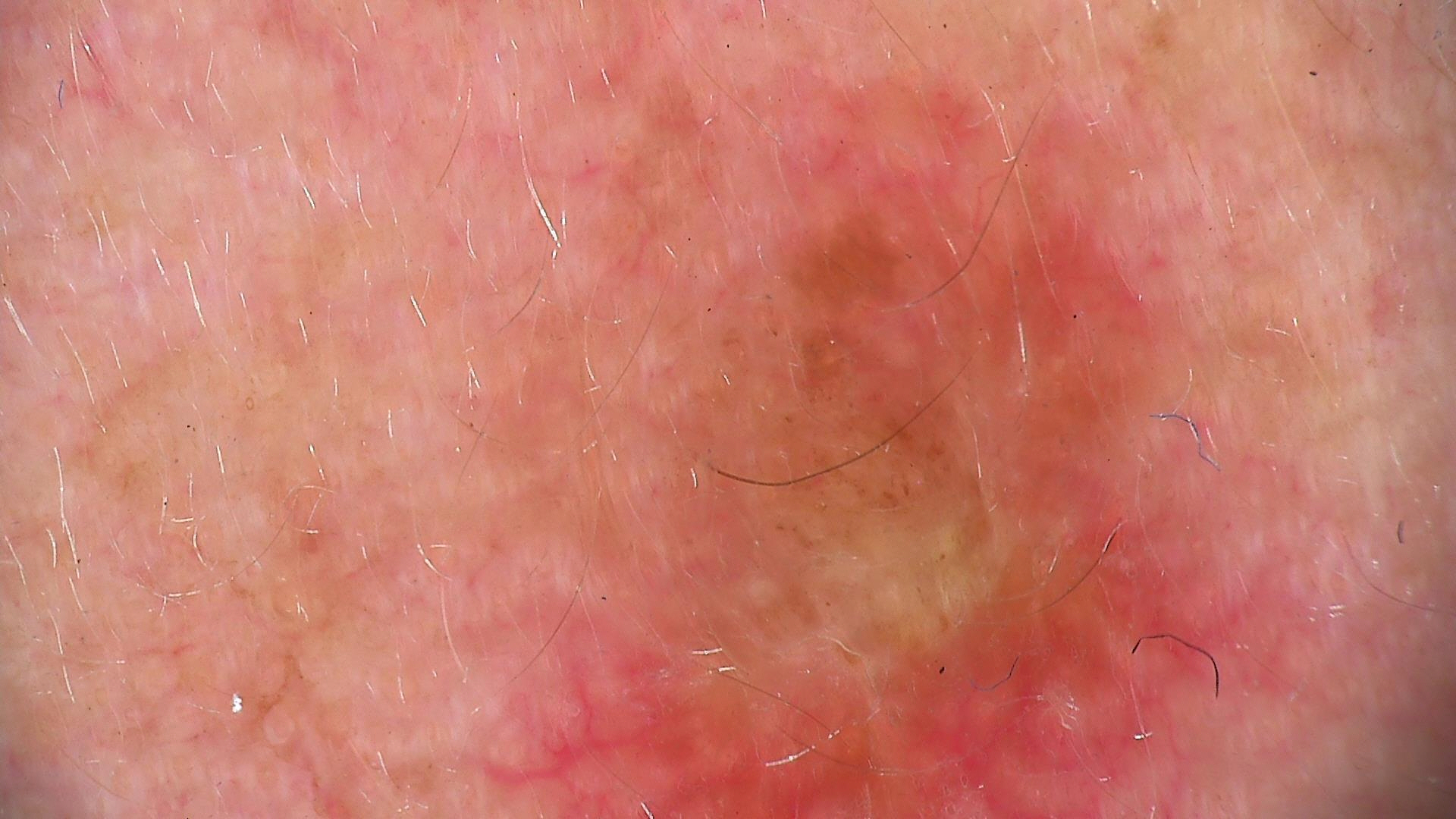Q: What is this lesion?
A: dermal nevus (expert consensus)